A dermoscopic photograph of a skin lesion.
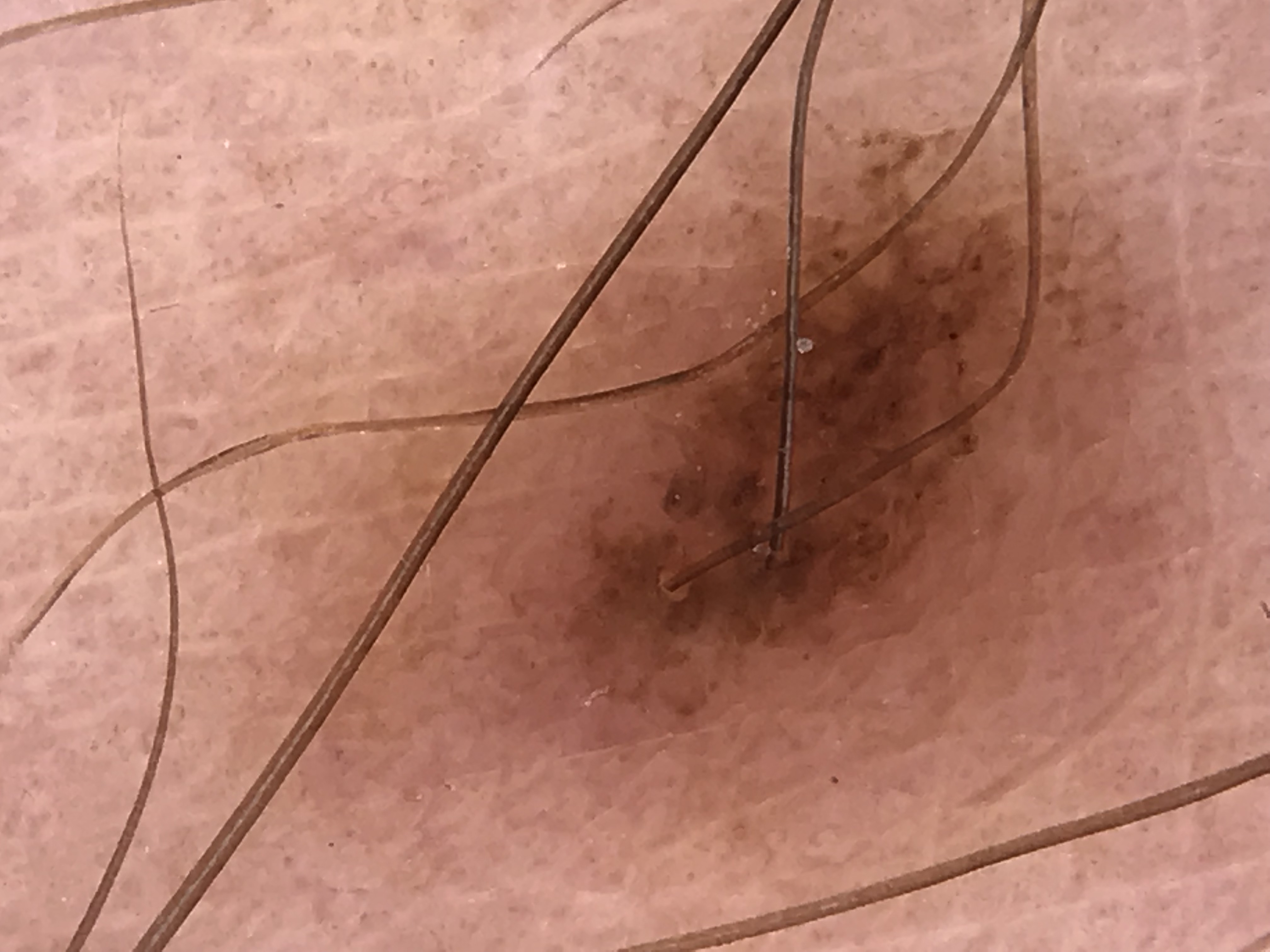The diagnosis was a dysplastic junctional nevus.